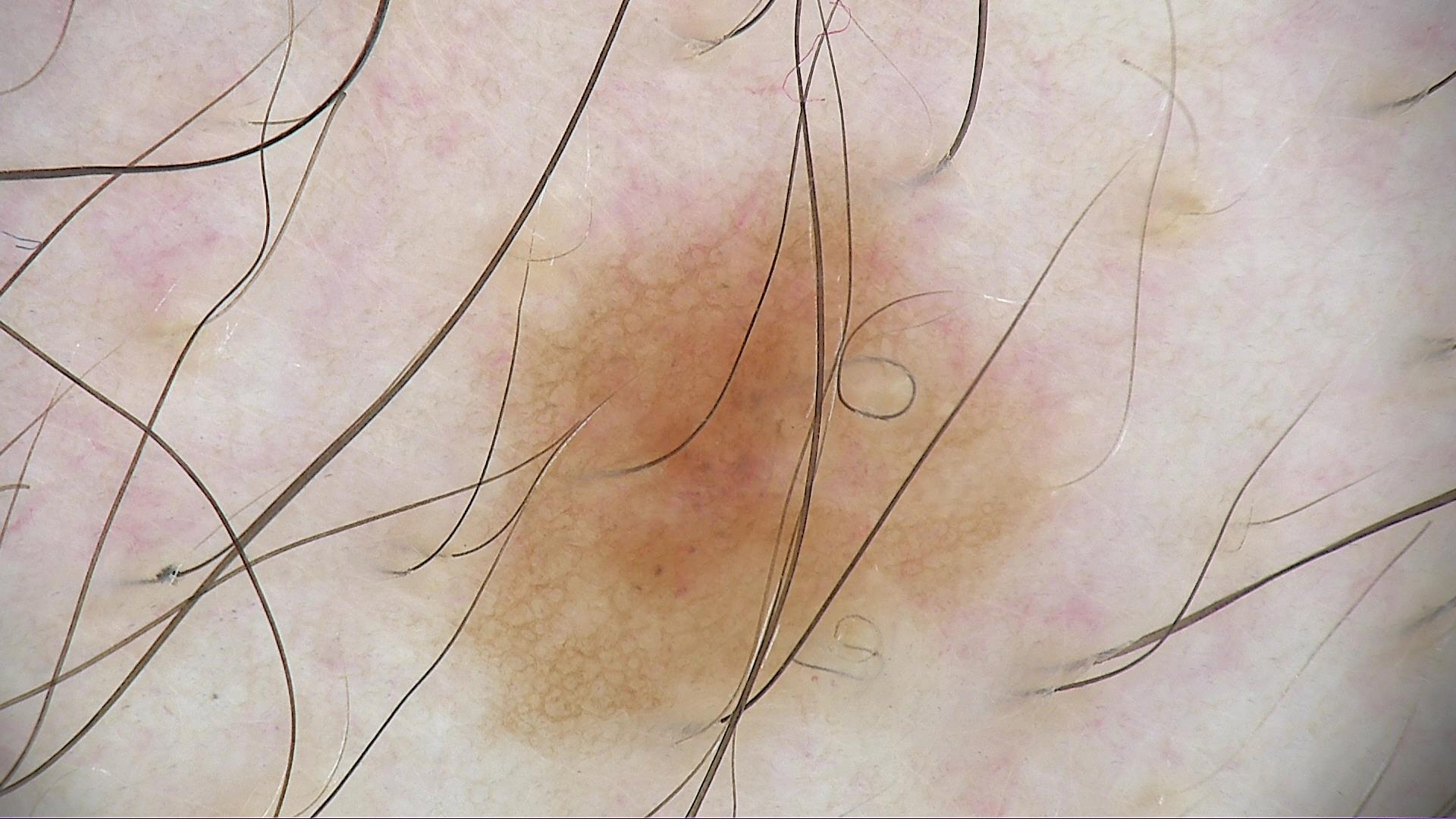Diagnosed as a dysplastic junctional nevus.